A female subject about 40 years old · a skin lesion imaged with a dermatoscope — 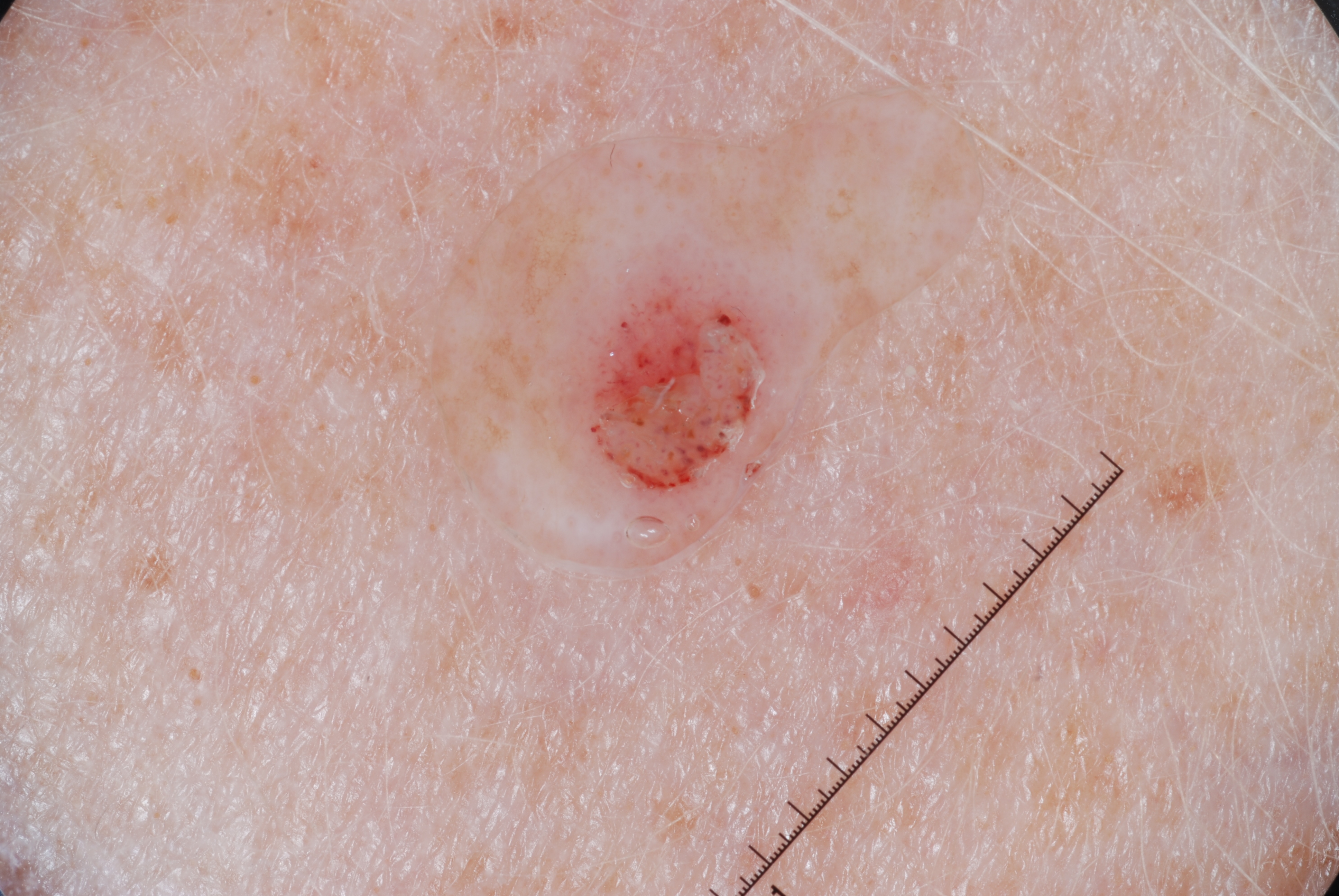Q: Which dermoscopic features were noted?
A: milia-like cysts; absent: streaks, negative network, and pigment network
Q: Lesion extent?
A: ~4% of the field
Q: What is the lesion's bounding box?
A: left=553, top=235, right=801, bottom=503
Q: What is the diagnosis?
A: a seborrheic keratosis, a non-melanocytic (keratinocytic) lesion